A skin lesion imaged with a dermatoscope.
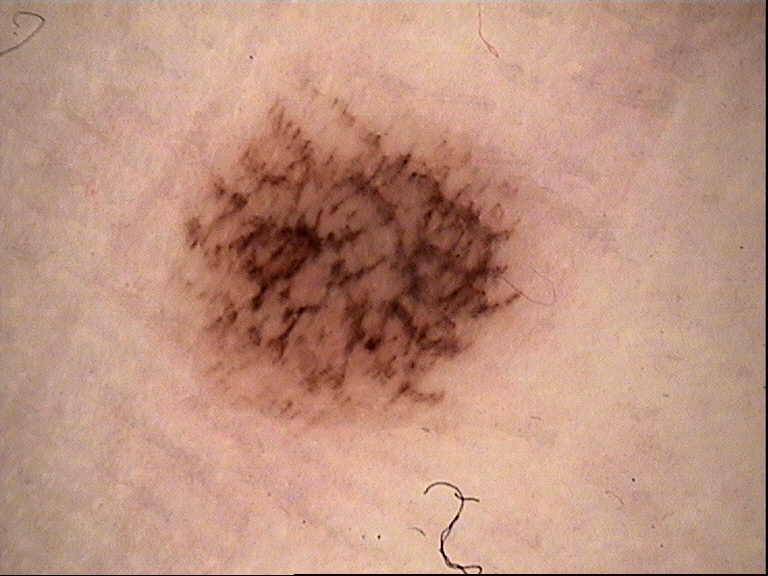Consistent with an acral dysplastic junctional nevus.